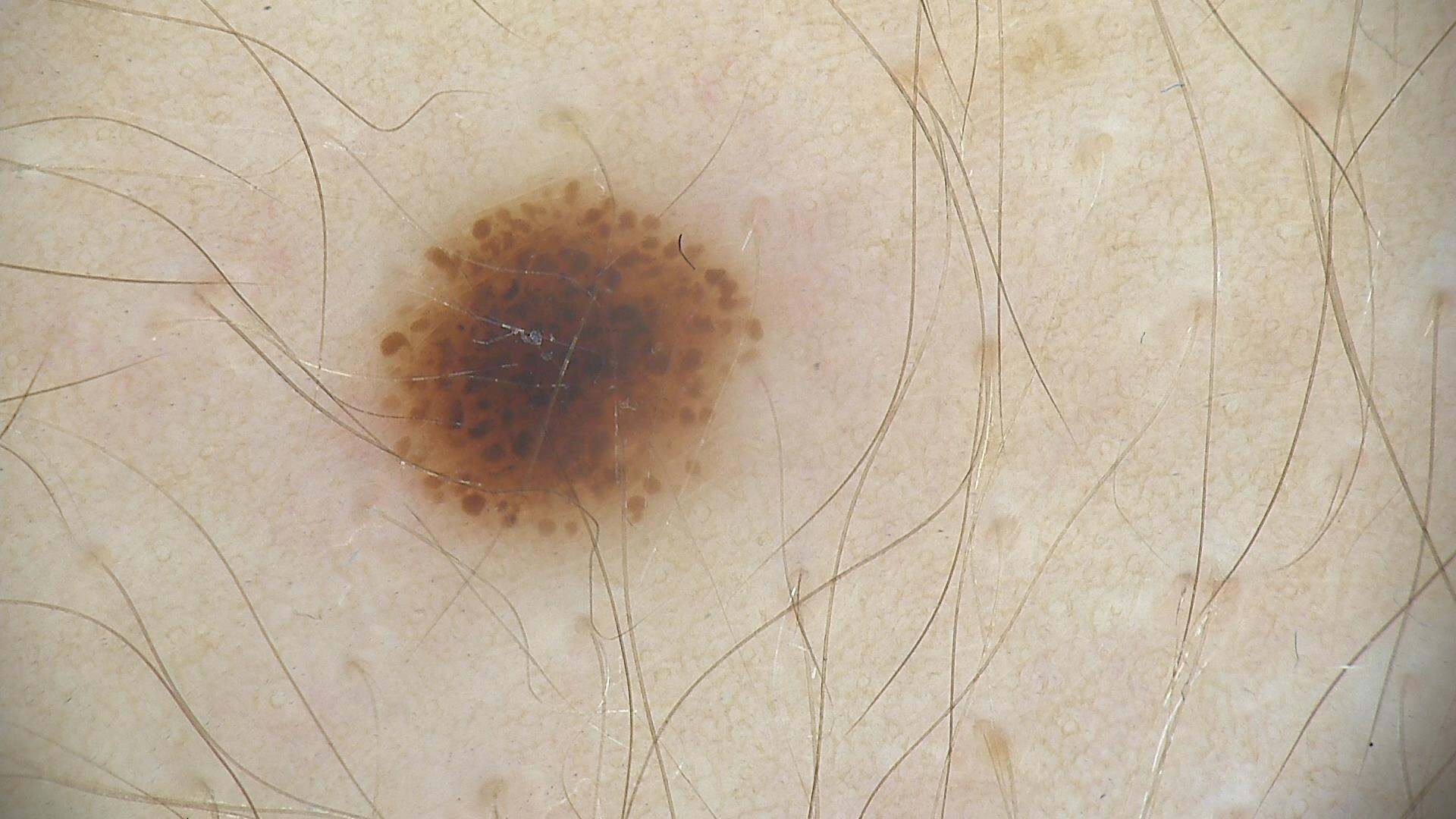A dermoscopic close-up of a skin lesion. Consistent with a benign lesion — a dysplastic junctional nevus.